The patient says their skin reddens with sun exposure · numerous moles by the patient's own estimate · by self-report, a history of sunbed use · imaged for a research study, with no referral diagnosis recorded · a female subject aged 26:
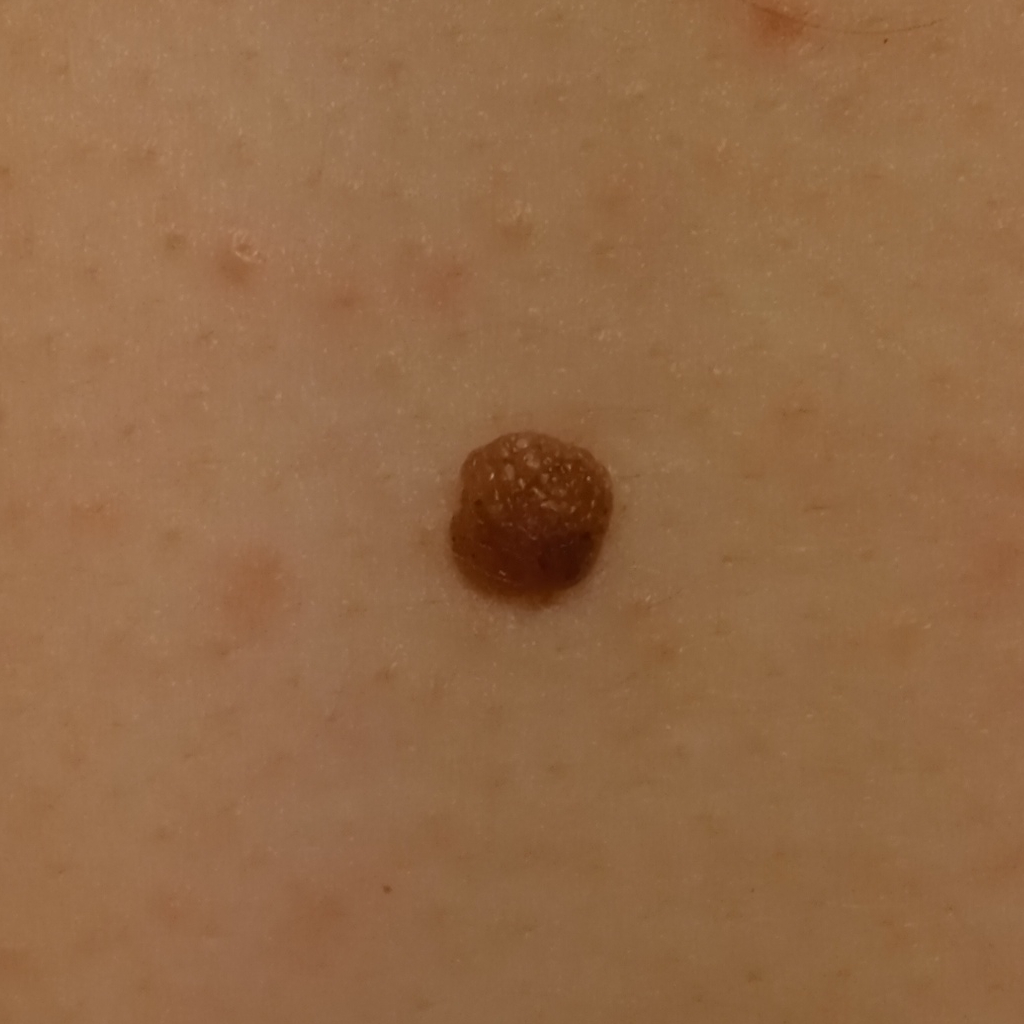{
  "lesion_size": {
    "diameter_mm": 5.6
  },
  "diagnosis": {
    "name": "melanocytic nevus",
    "malignancy": "benign"
  }
}